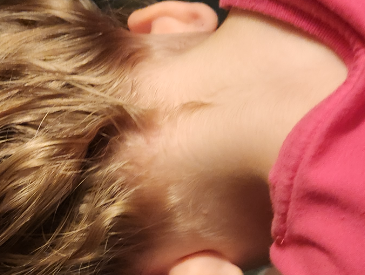Findings:
– assessment · indeterminate from the photograph
– framing · at a distance
– lesion texture · flat
– anatomic site · head or neck
– lesion symptoms · itching
– symptom duration · about one day